A dermoscopy image of a single skin lesion.
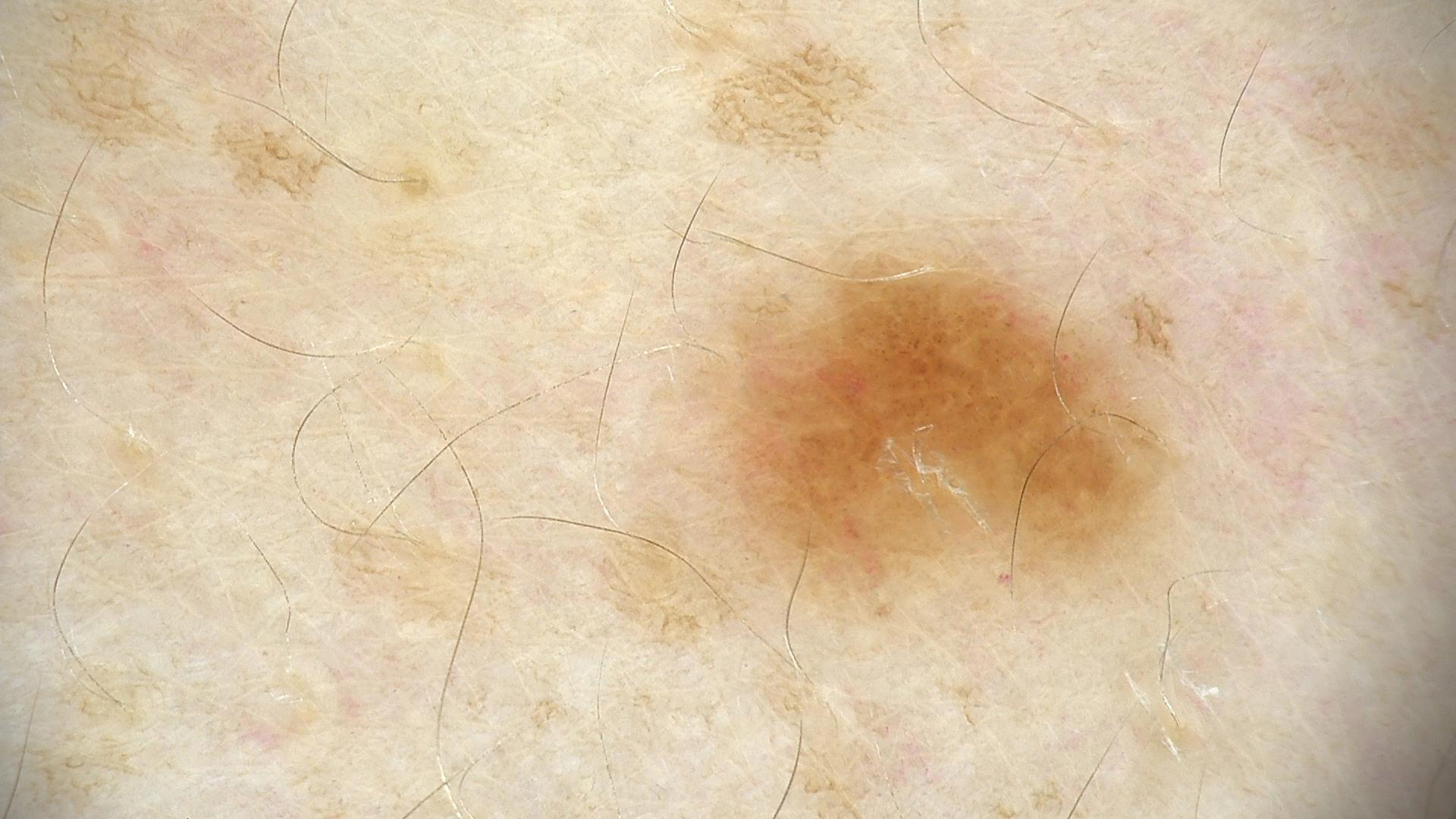Classified as a benign lesion — a dysplastic junctional nevus.